Close-up view: 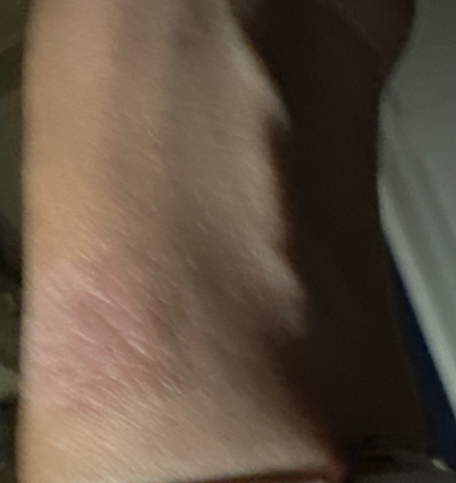{
  "differential": {
    "tied_lead": [
      "Allergic Contact Dermatitis",
      "Irritant Contact Dermatitis"
    ]
  }
}